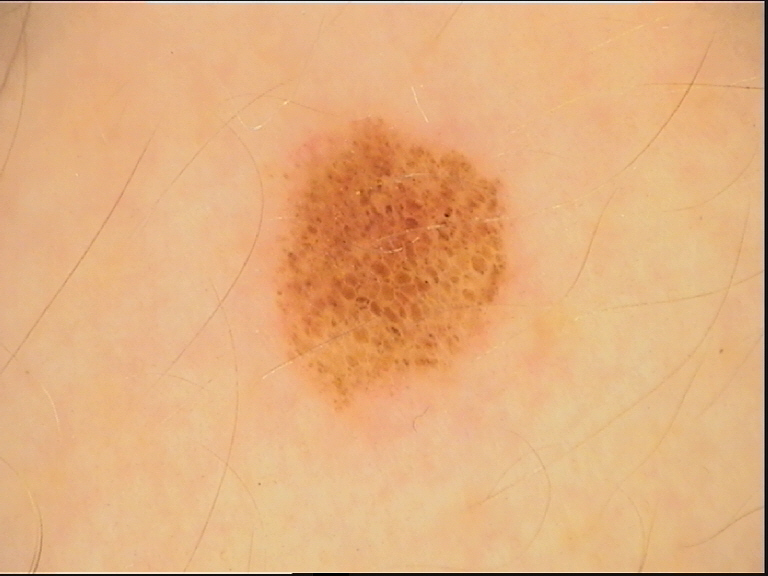assessment: dysplastic compound nevus (expert consensus).